A dermoscopy image of a single skin lesion: 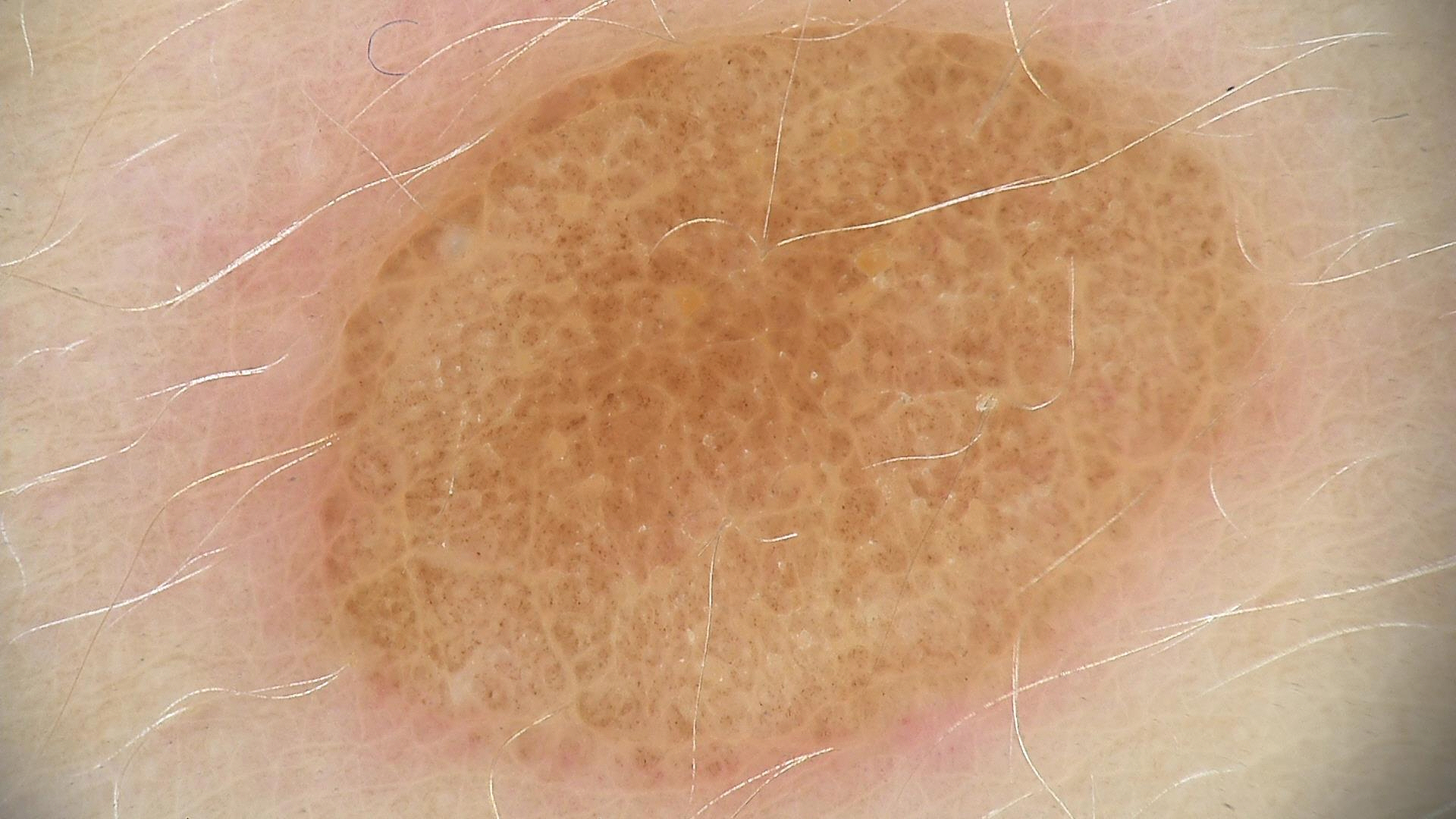Conclusion:
Classified as a banal lesion — a compound nevus.